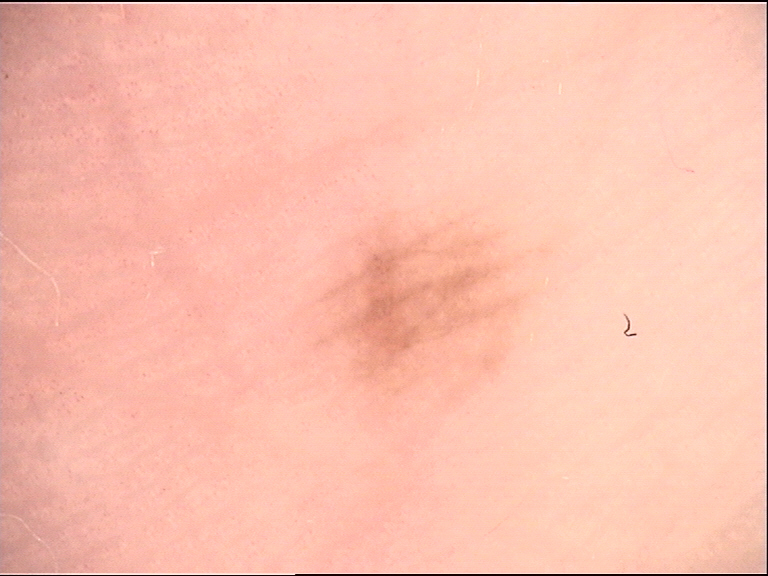Conclusion:
Labeled as a banal lesion — an acral junctional nevus.